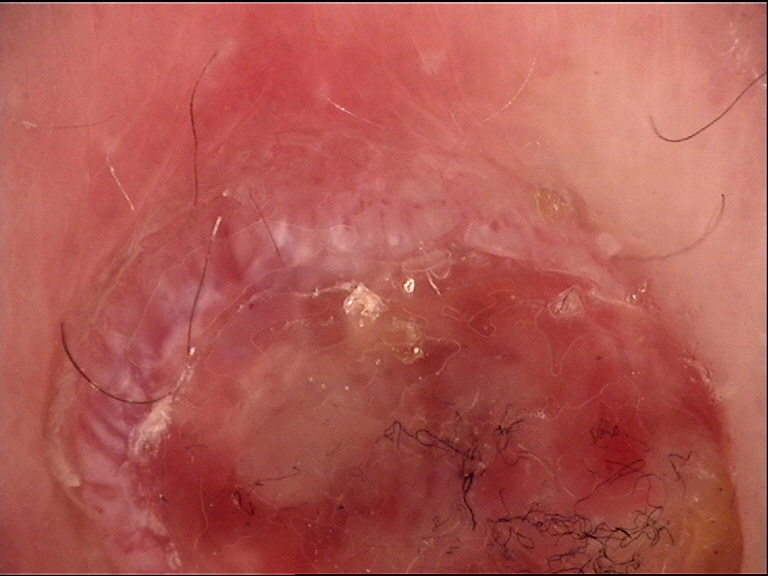Histopathology confirmed a Kaposi sarcoma.